A dermoscopic photograph of a skin lesion:
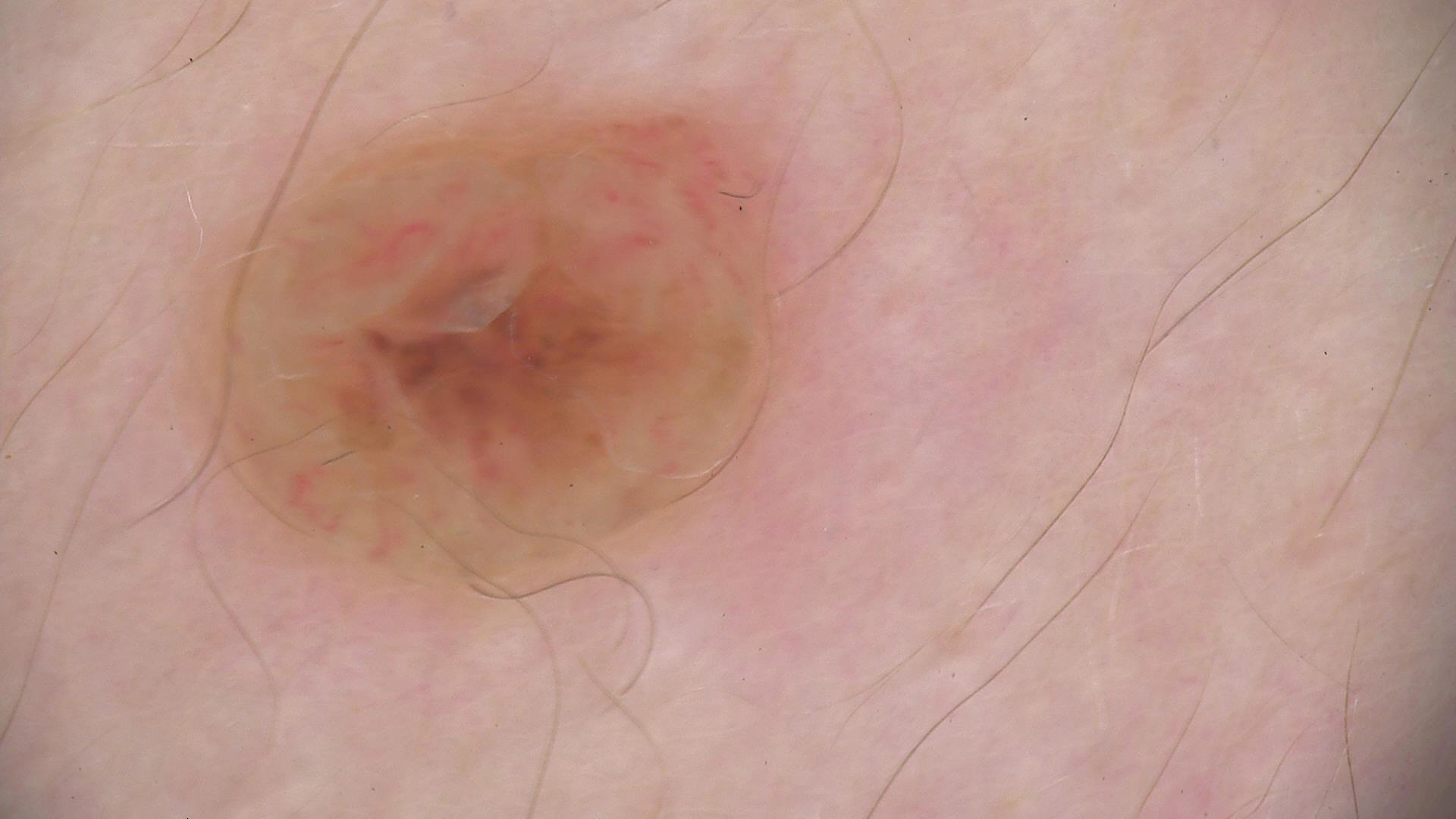{"diagnosis": {"name": "dermal nevus", "code": "db", "malignancy": "benign", "super_class": "melanocytic", "confirmation": "expert consensus"}}